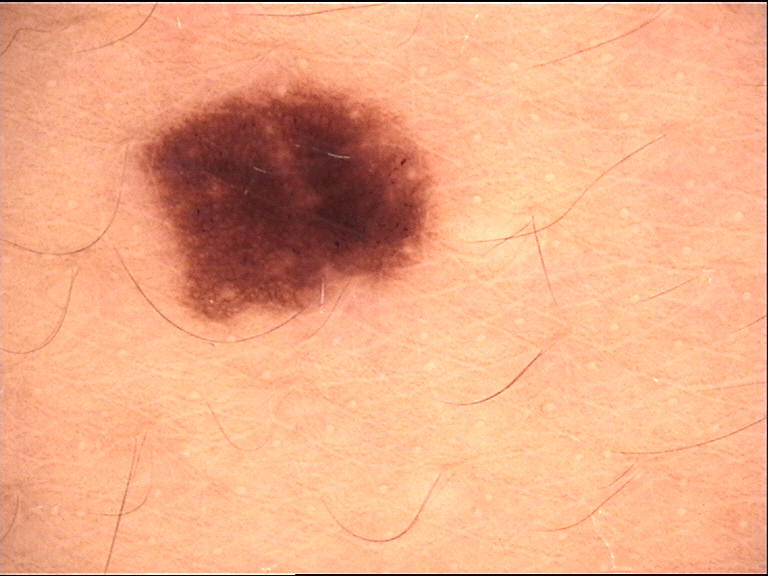Diagnosed as a banal lesion — a junctional nevus.